A female patient age 55; by self-report, immunosuppression and a prior organ transplant; a dermoscopy image of a skin lesion; the patient describes having a moderate number of moles.
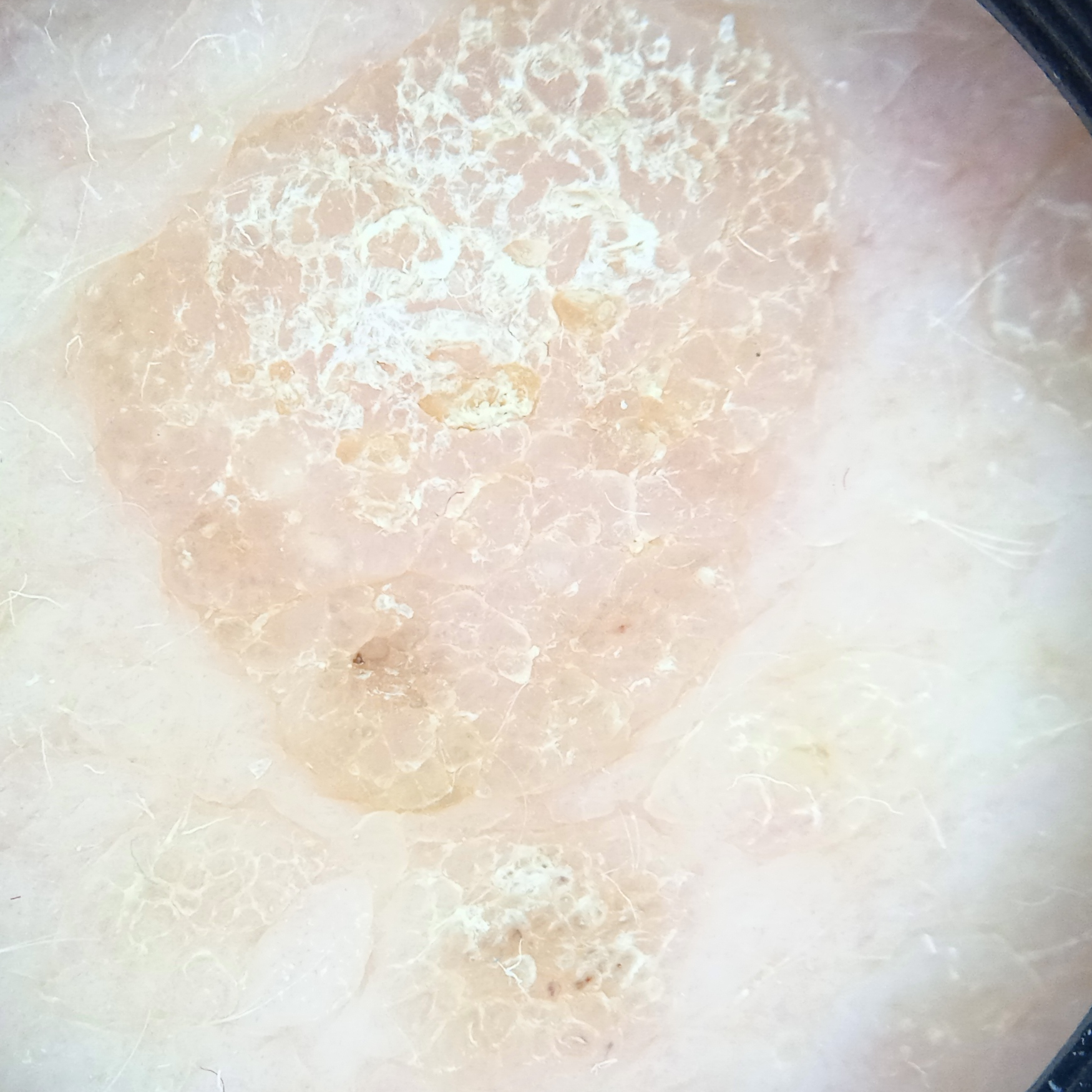location — the back | diameter — 10.6 mm | assessment — seborrheic keratosis (dermatologist consensus).